A dermoscopic view of a skin lesion; a male patient in their mid-60s — 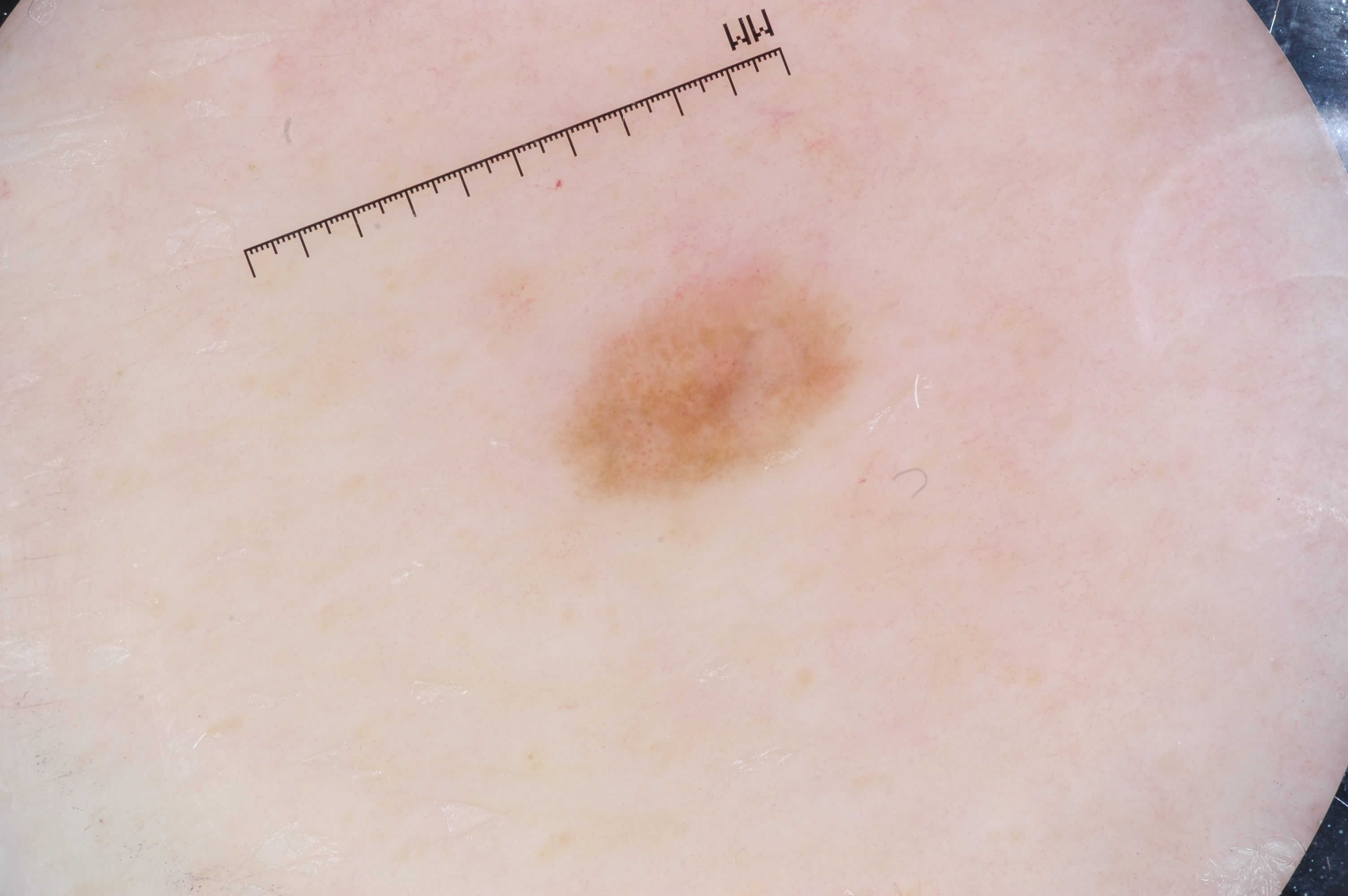Q: What dermoscopic features are present?
A: negative network; absent: streaks, pigment network, and milia-like cysts
Q: What is the lesion's bounding box?
A: (550, 251, 863, 506)
Q: What is this lesion?
A: a melanoma, a malignant skin lesion